A skin lesion imaged with a dermatoscope.
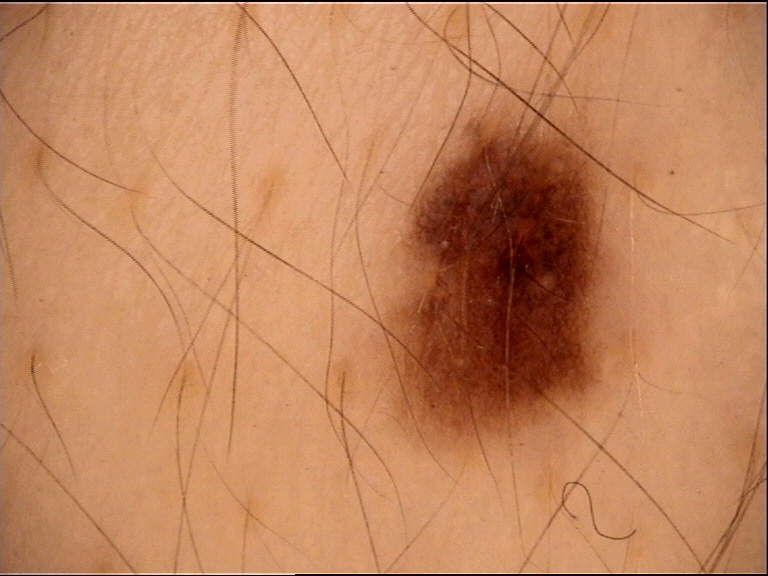subtype: banal; assessment: junctional nevus (expert consensus).